Close-up view: 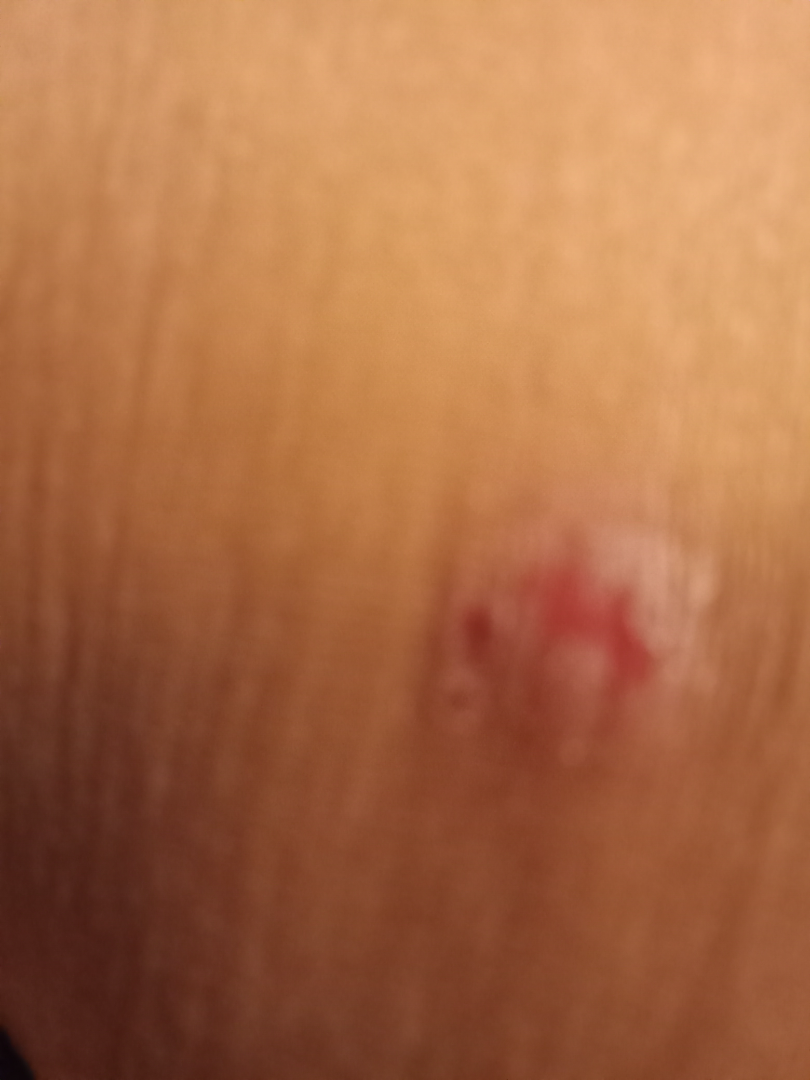{"assessment": "indeterminate from the photograph"}